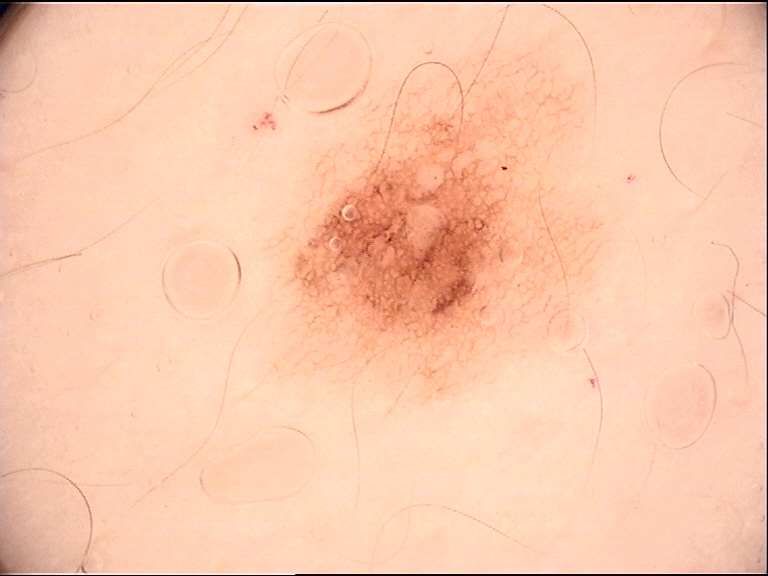assessment: dysplastic junctional nevus (expert consensus).